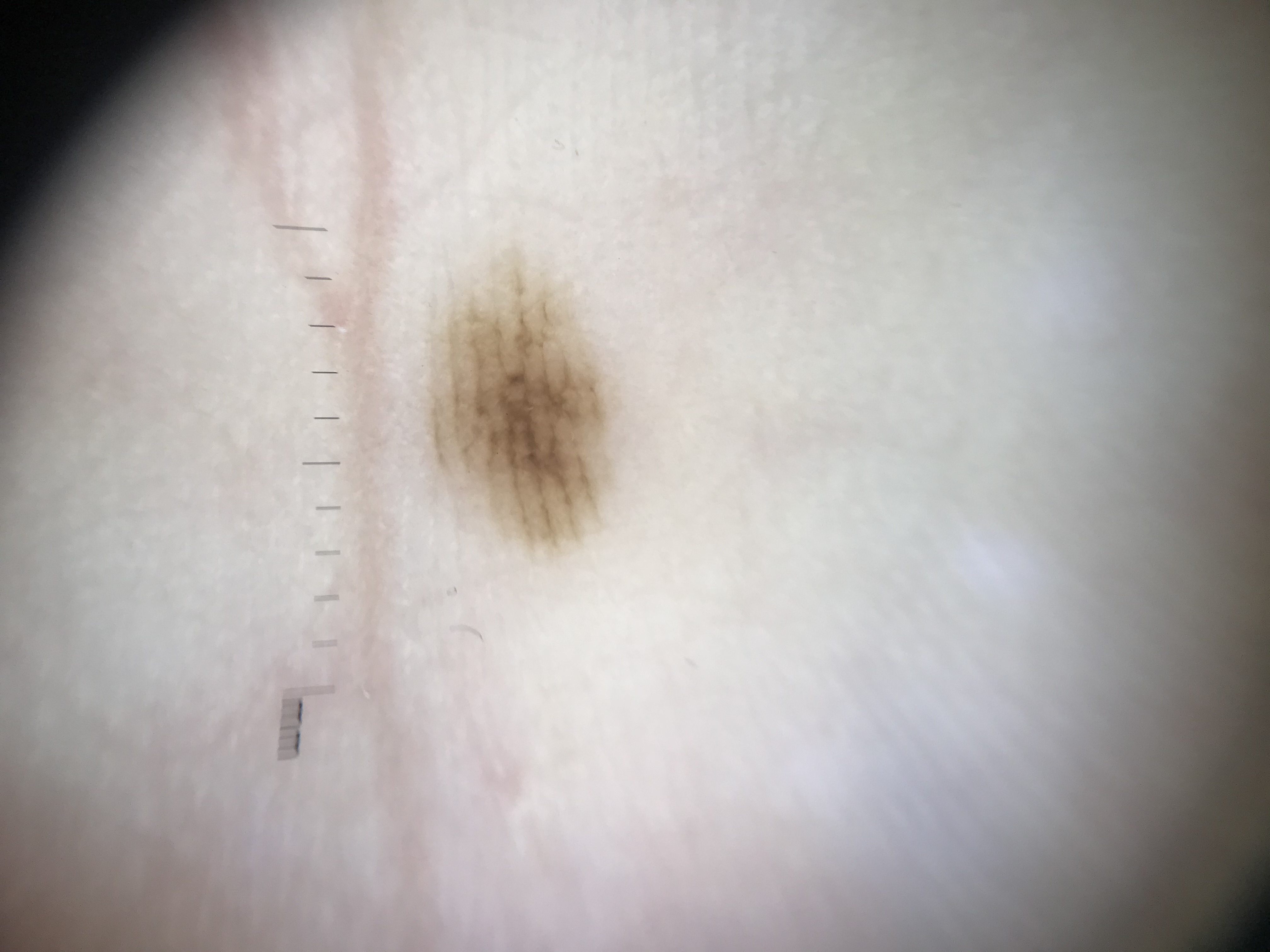A dermoscopy image of a single skin lesion. The architecture is that of a banal lesion. The diagnosis was an acral junctional nevus.